Reported lesion symptoms include itching and bothersome appearance · the patient described the issue as a rash · an image taken at an angle · the head or neck and front of the torso are involved · the patient is a female aged 30–39 · present for less than one week:
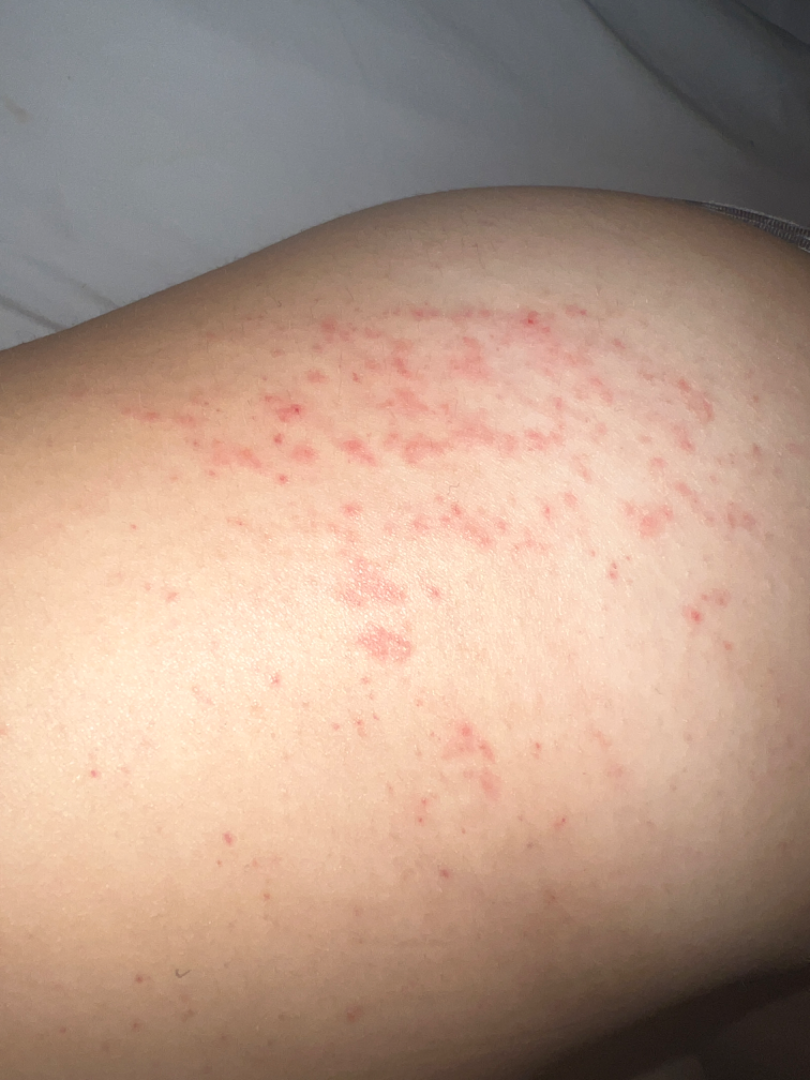Case summary:
- differential diagnosis — most consistent with Allergic Contact Dermatitis; an alternative is Eczema; with consideration of Leukocytoclastic Vasculitis